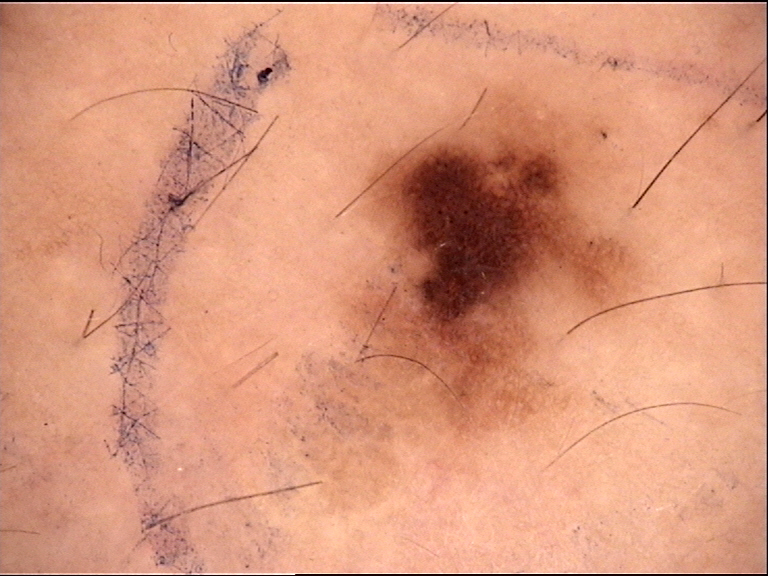Diagnosed as a dysplastic junctional nevus.